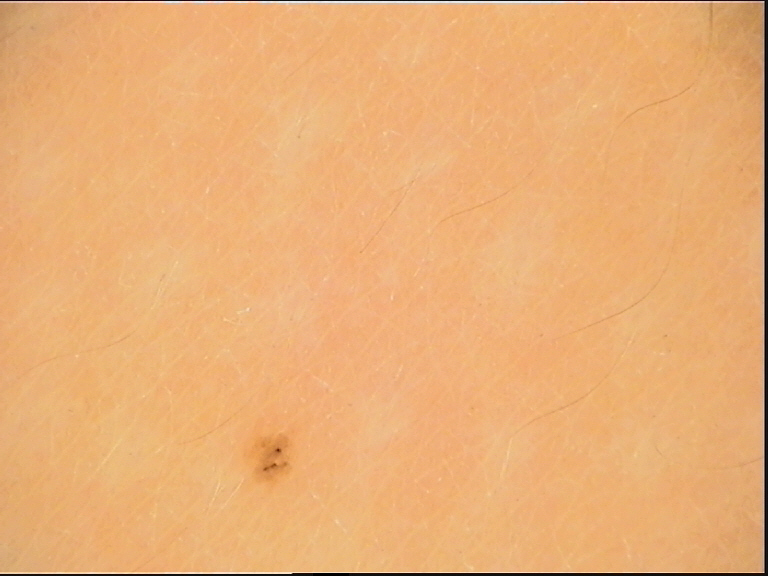assessment: dysplastic junctional nevus (expert consensus).